A close-up photograph:
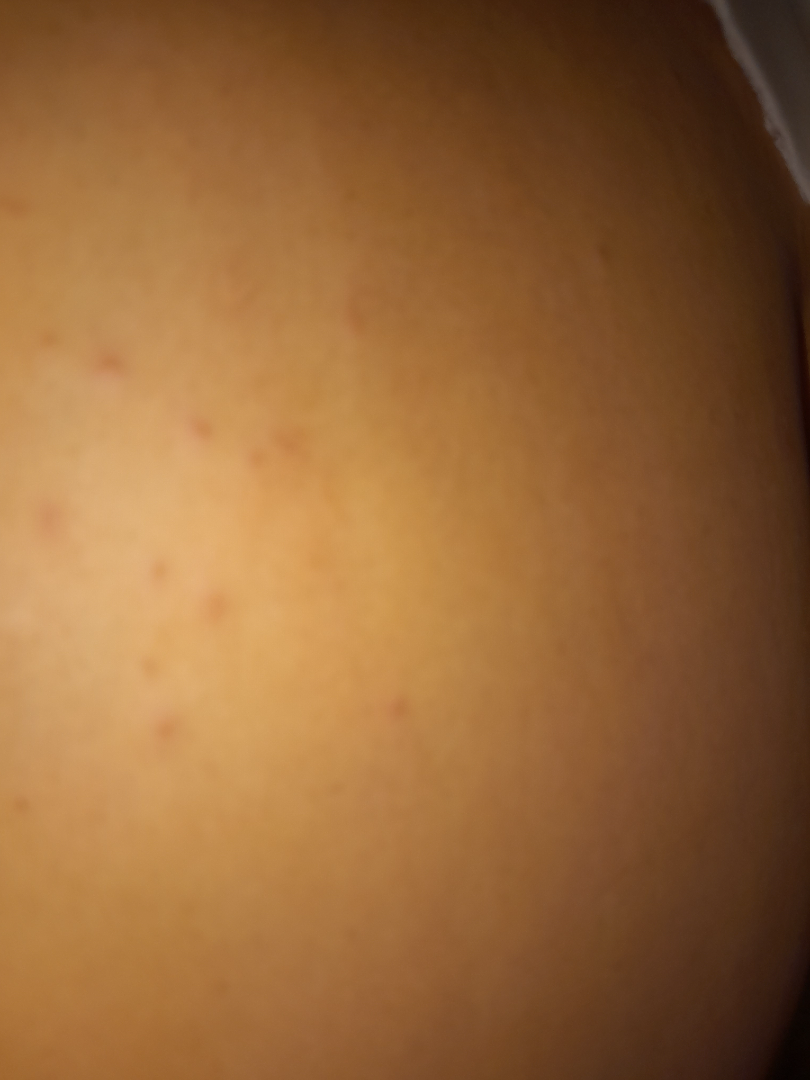The skin findings could not be characterized from the image.